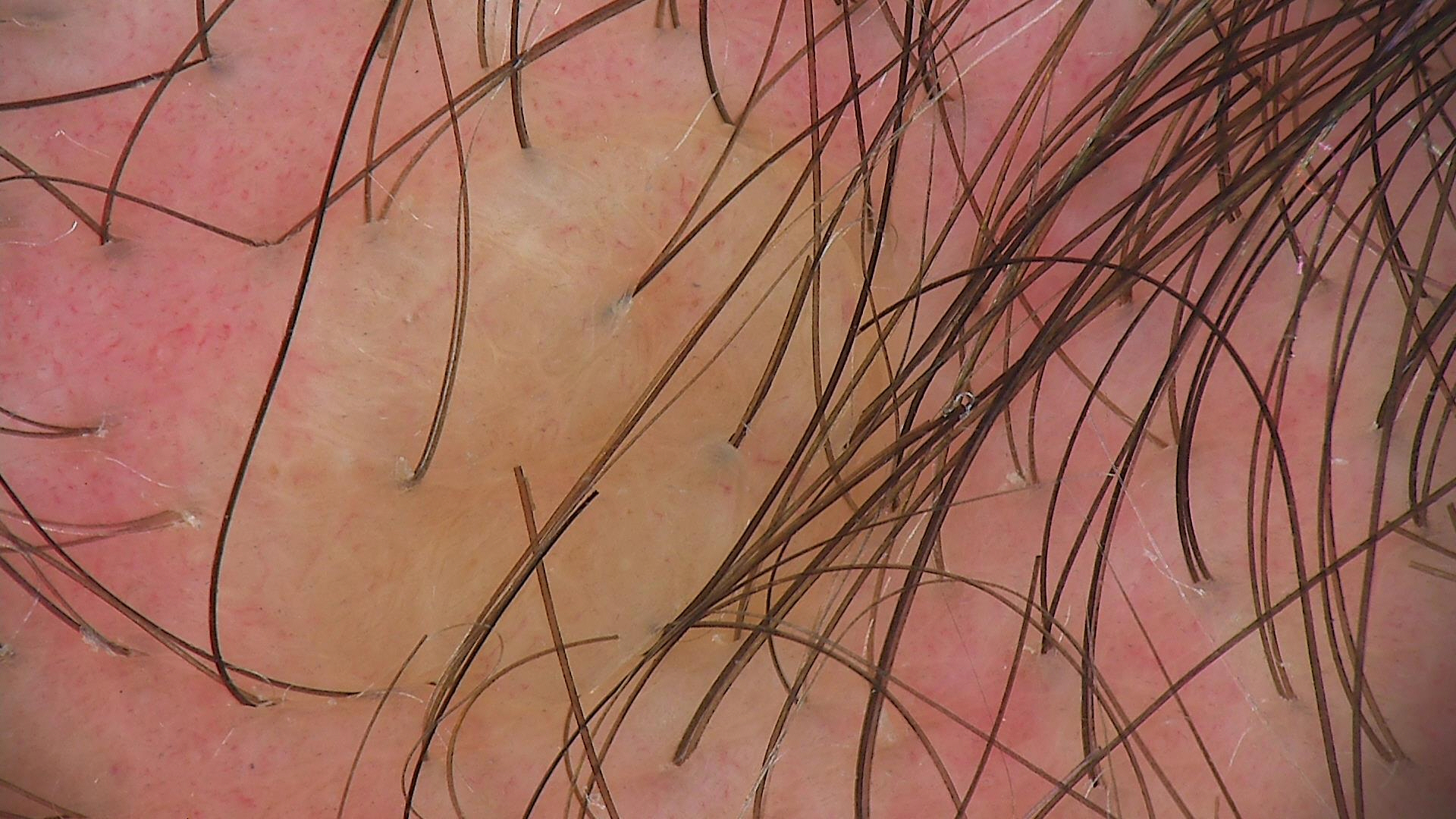image type: dermatoscopy, assessment: dermal nevus (expert consensus).